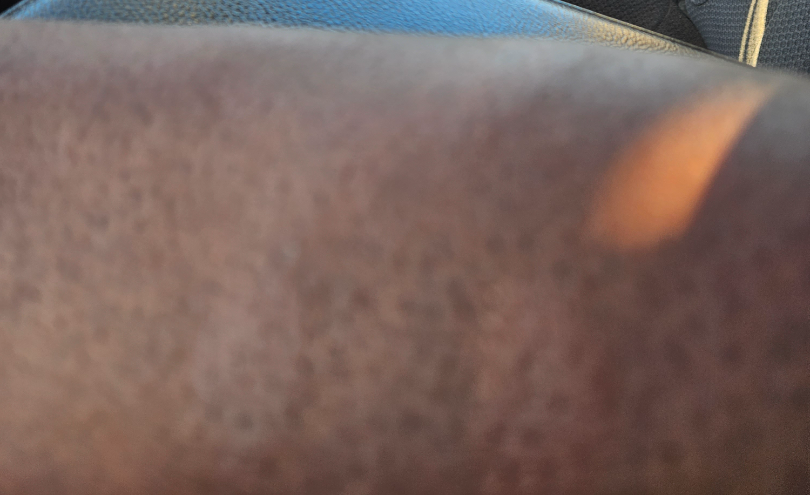The case was indeterminate on photographic review. The contributor reports itching. The patient is a male aged 40–49. The photo was captured at an angle. The lesion is described as raised or bumpy. Skin tone: Fitzpatrick V; lay reviewers estimated Monk Skin Tone 8 (US pool) or 5 (India pool). The lesion involves the arm and head or neck.